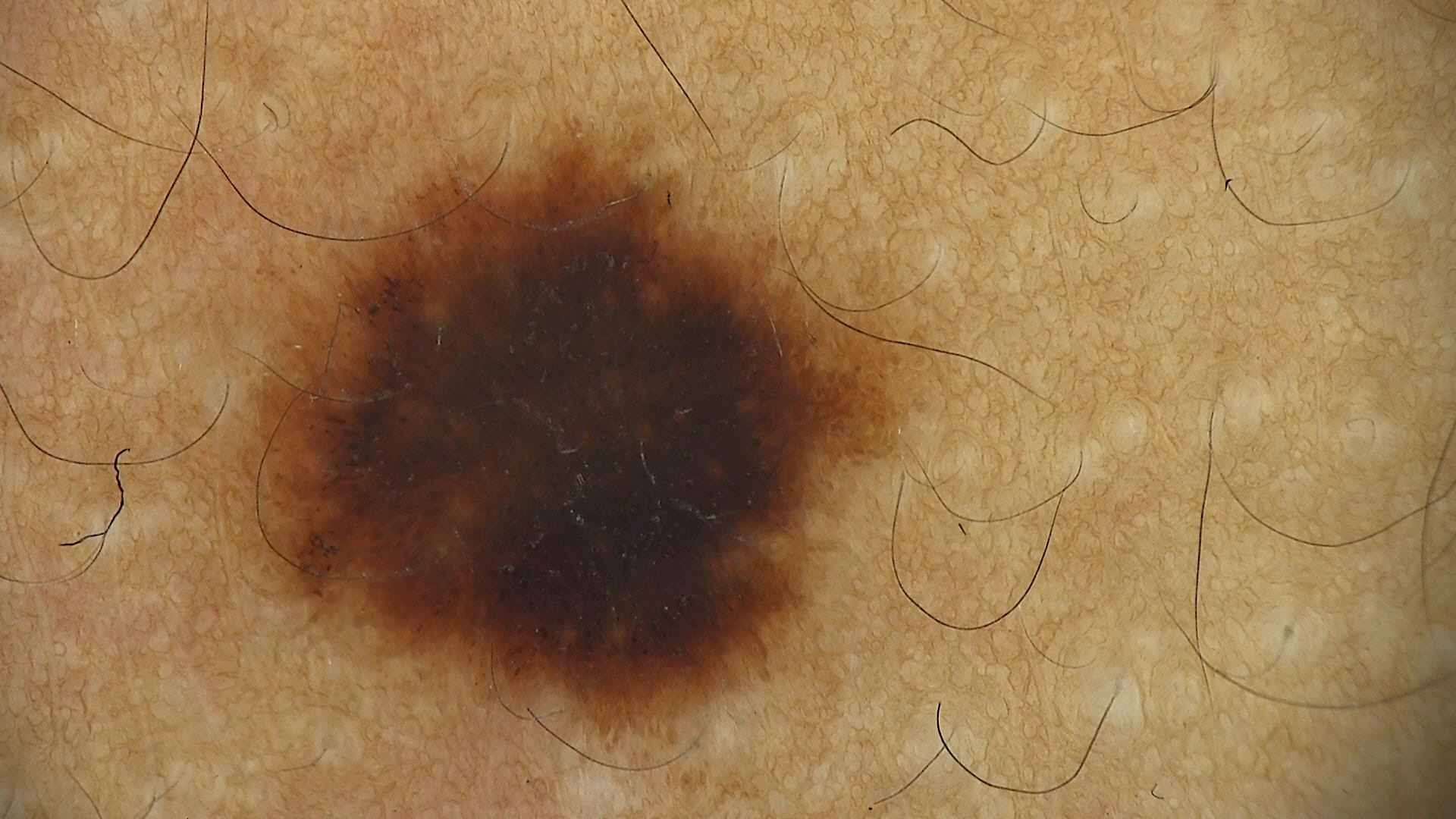Conclusion: Histopathologically confirmed as a melanoma.